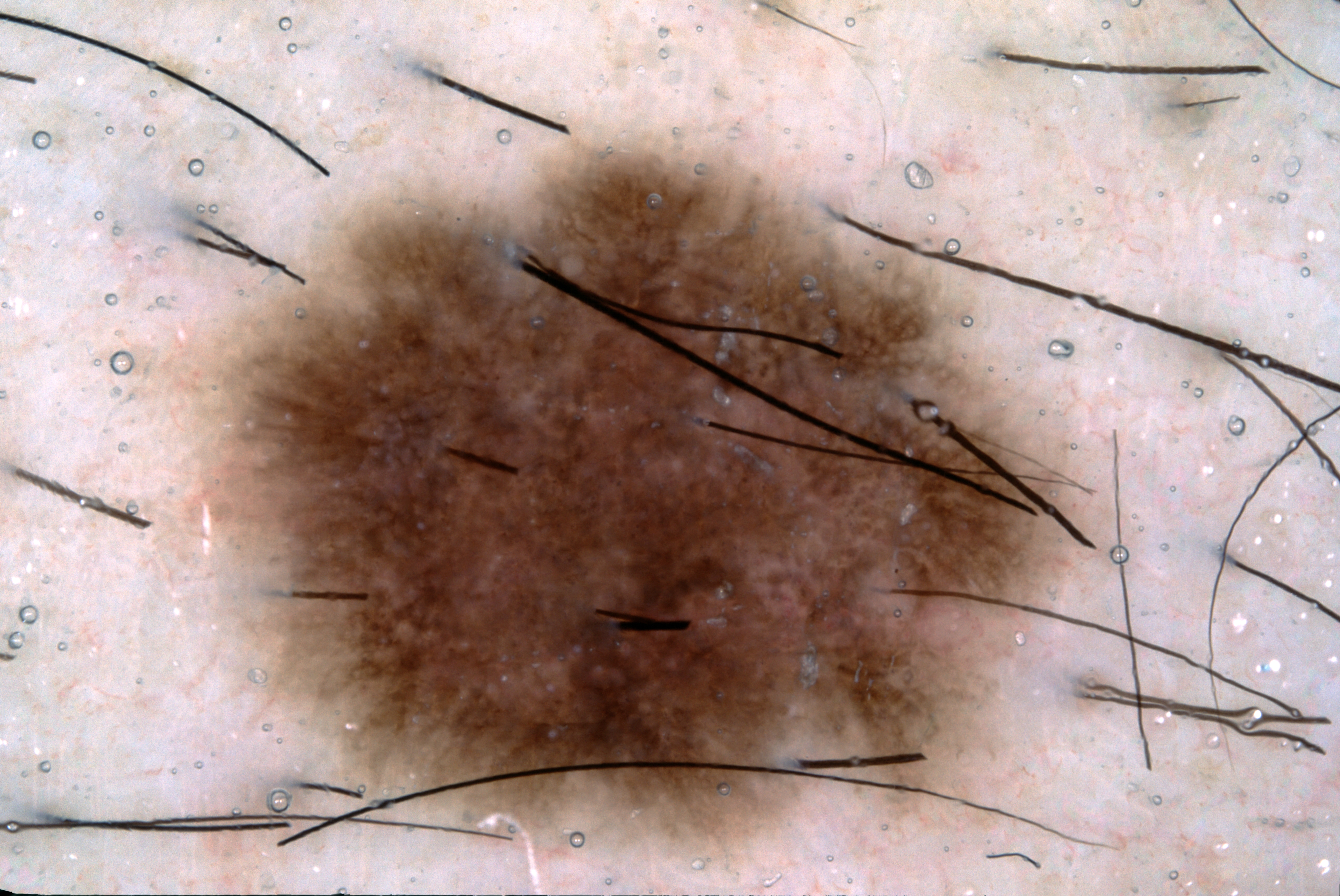image = dermatoscopic image of a skin lesion; patient = male, about 30 years old; bounding box = (209, 147, 1089, 854); dermoscopic pattern = pigment network and negative network; diagnostic label = a melanocytic nevus.